A dermatoscopic image of a skin lesion: 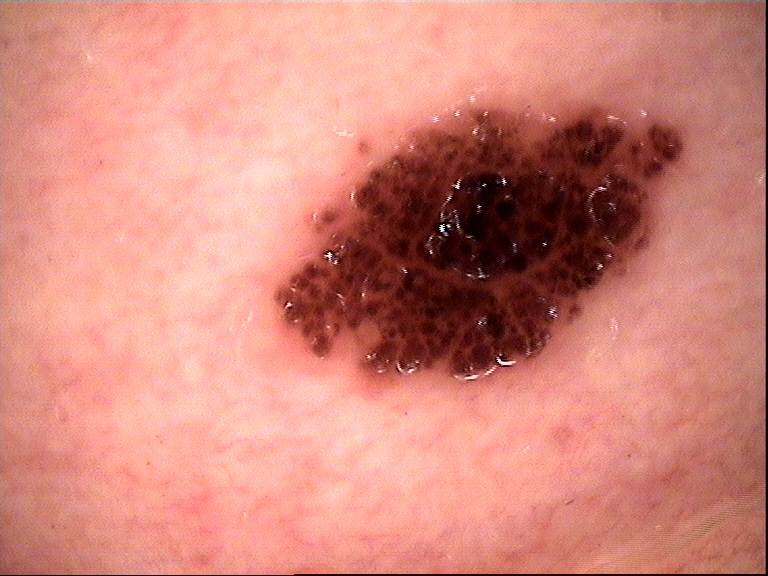Conclusion:
Diagnosed as a benign lesion — a dysplastic compound nevus.